A dermoscopy image of a single skin lesion: 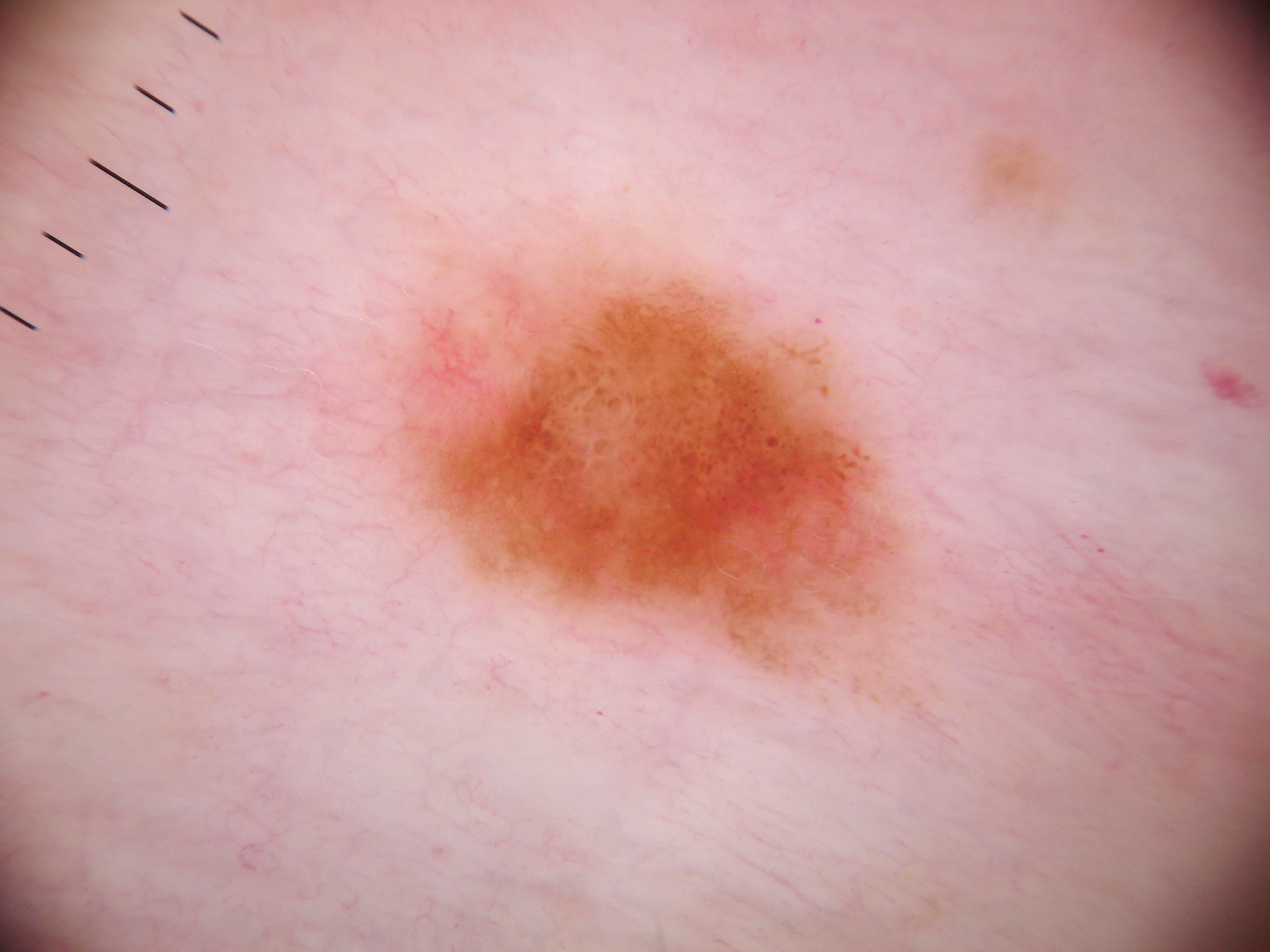Q: Which dermoscopic features were noted?
A: streaks, pigment network, negative network, and globules; absent: milia-like cysts
Q: What is the lesion's bounding box?
A: 345 189 957 758
Q: Lesion extent?
A: ~20% of the field
Q: What did the assessment conclude?
A: a melanocytic nevus, a benign skin lesion